The photograph is a close-up of the affected area; the patient reports itching and enlargement; the patient described the issue as a rash; the subject is a female aged 60–69; the affected area is the arm: 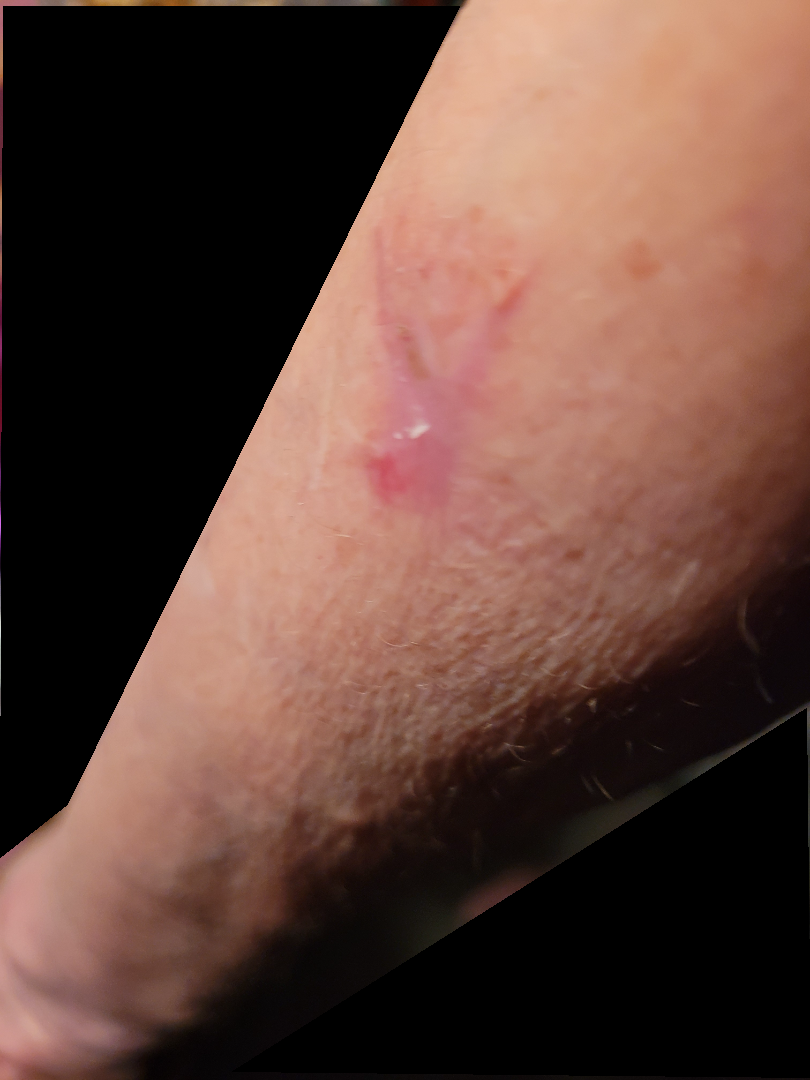impression: most consistent with Scar Condition